A smartphone photograph of a skin lesion; a patient in their mid-60s: 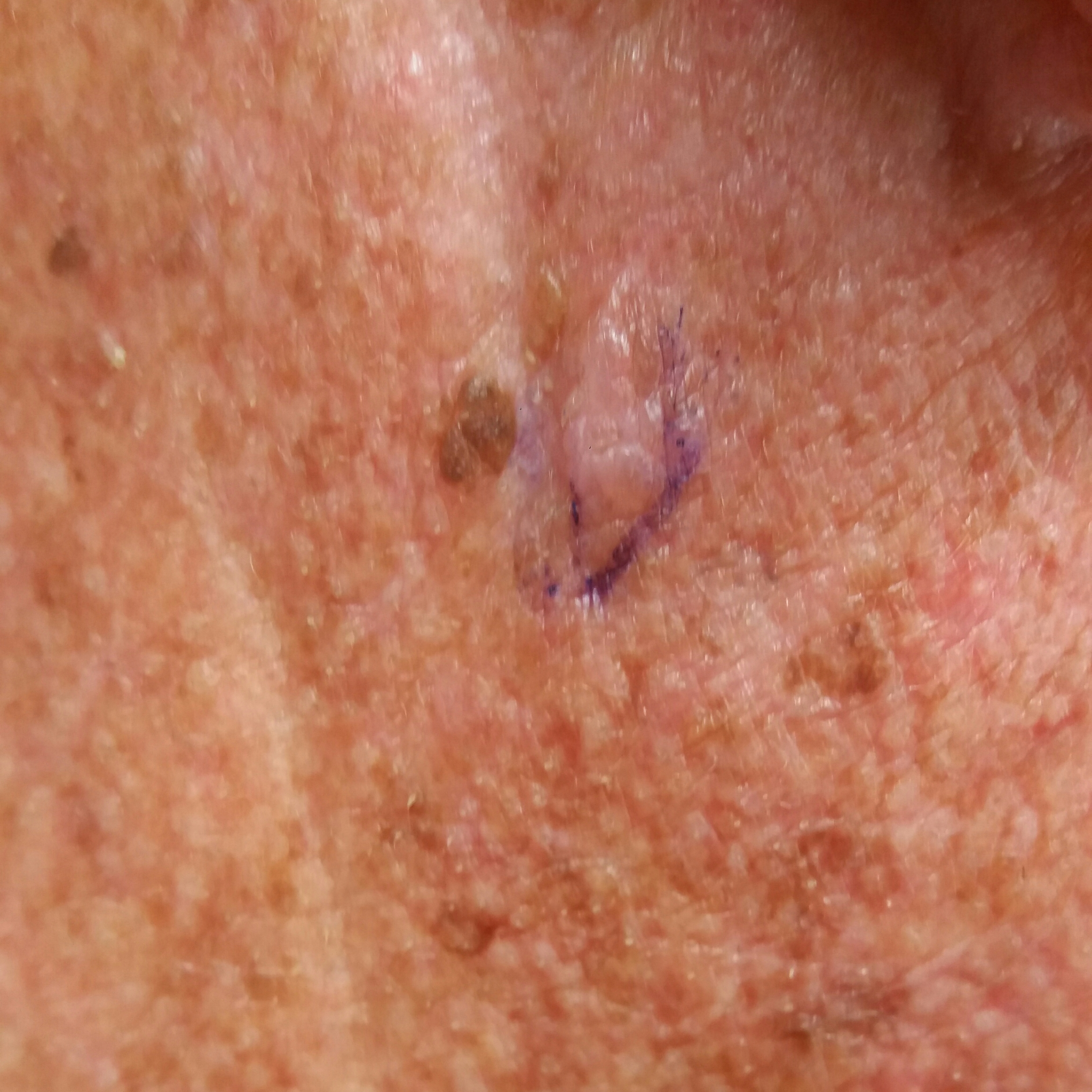Findings: The lesion was found on the neck. The patient describes that the lesion hurts and itches. Conclusion: Diagnosed by dermatologist consensus as a lesion of indeterminate malignant potential — an actinic keratosis.